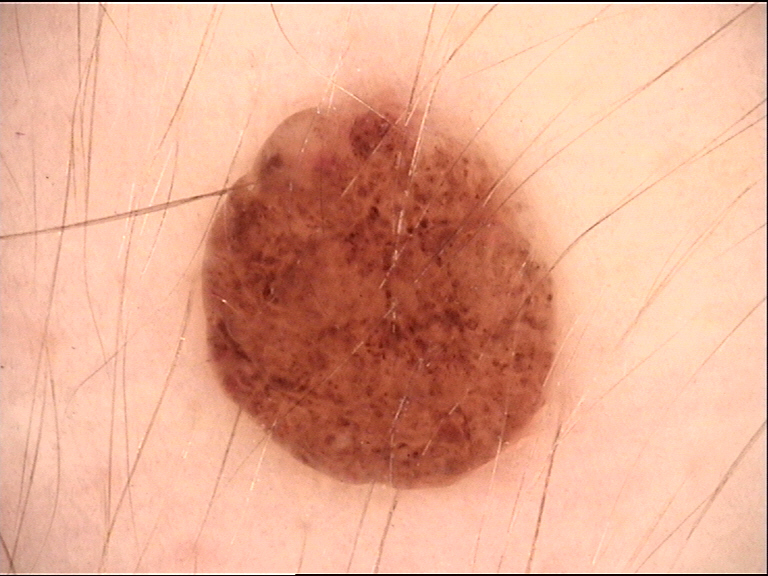- lesion type — banal
- diagnosis — compound nevus (expert consensus)